A close-up photograph. The lesion involves the leg:
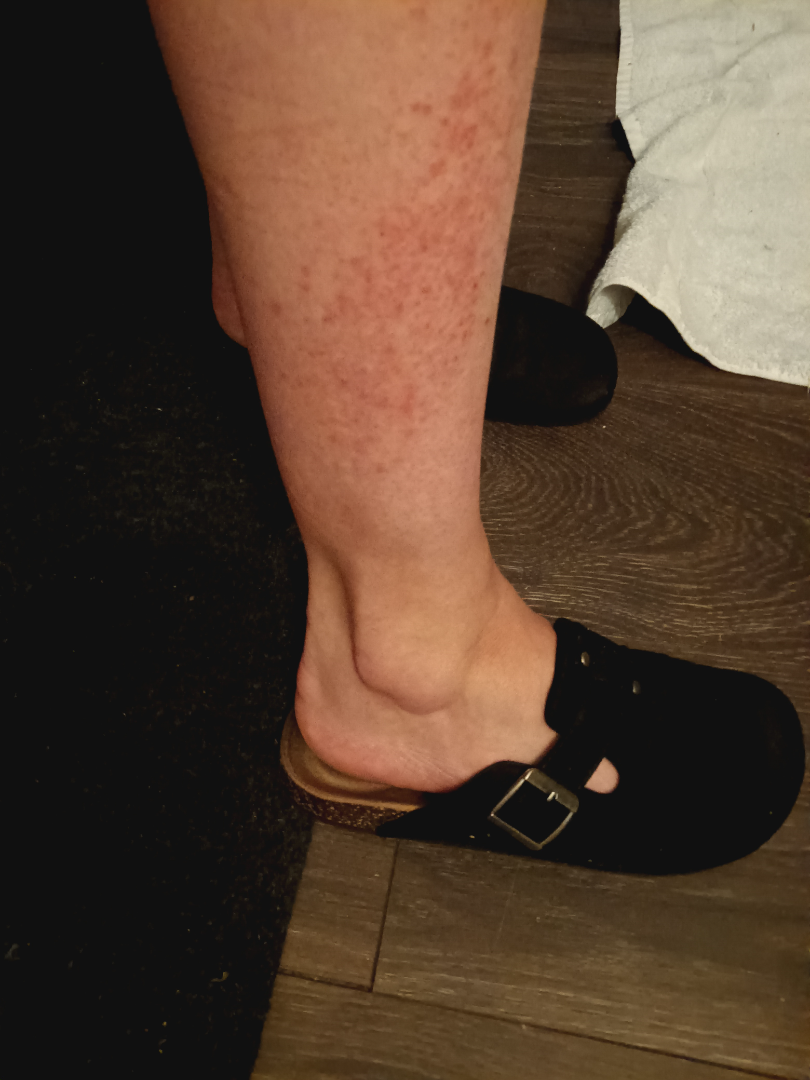{"assessment": "not assessable"}